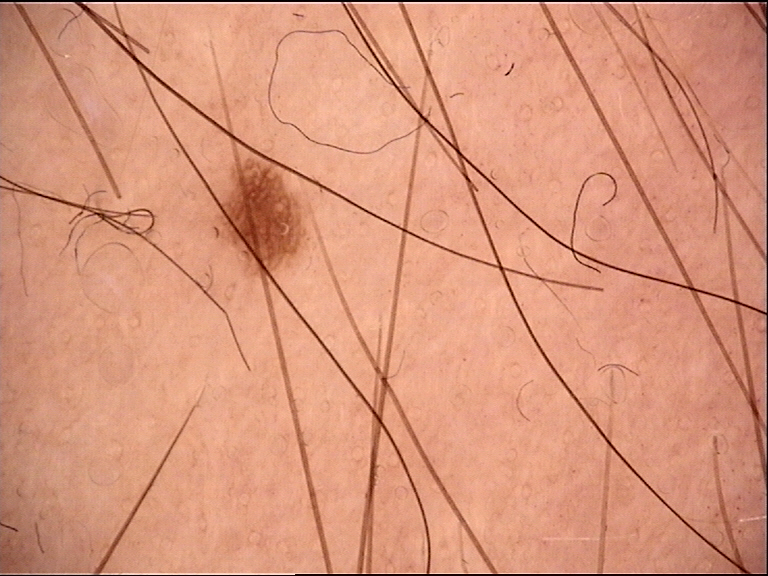<lesion>
<image>dermoscopy</image>
<lesion_type>
<main_class>banal</main_class>
<pattern>junctional</pattern>
</lesion_type>
<diagnosis>
<name>junctional nevus</name>
<code>jb</code>
<malignancy>benign</malignancy>
<super_class>melanocytic</super_class>
<confirmation>expert consensus</confirmation>
</diagnosis>
</lesion>